A dermoscopic view of a skin lesion, the patient is a female aged 23-27:
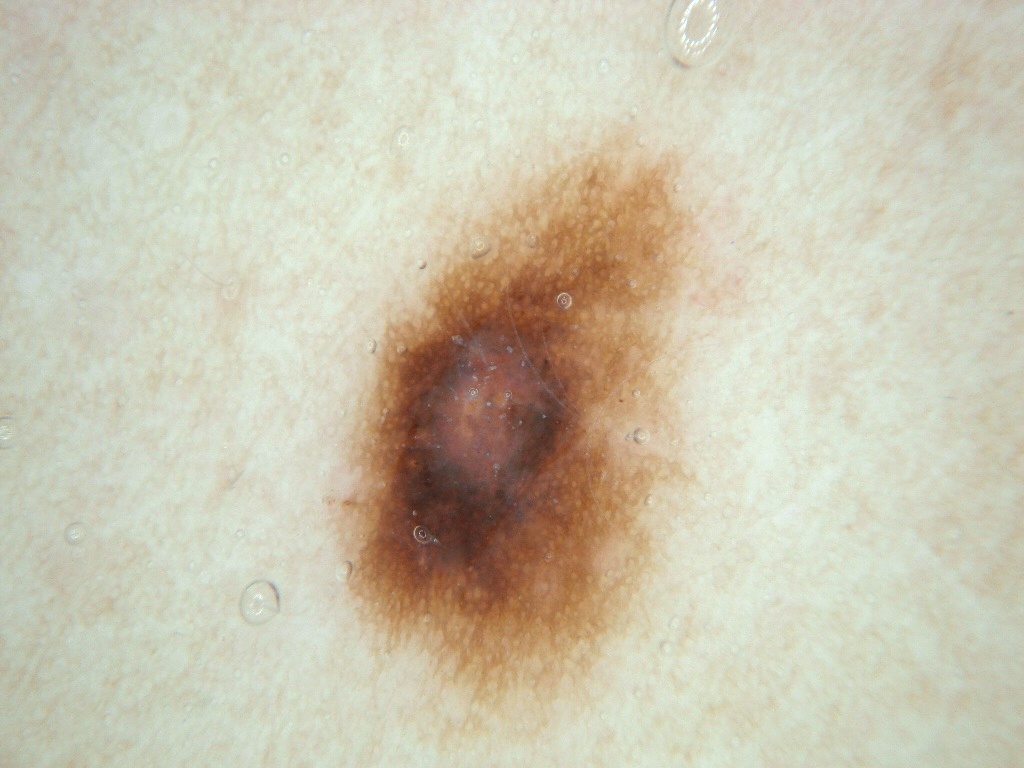In (x1, y1, x2, y2) order, the lesion occupies the region <bbox>313, 109, 725, 730</bbox>. A moderately sized lesion. Dermoscopic examination shows pigment network. The lesion was assessed as a melanocytic nevus, a benign skin lesion.